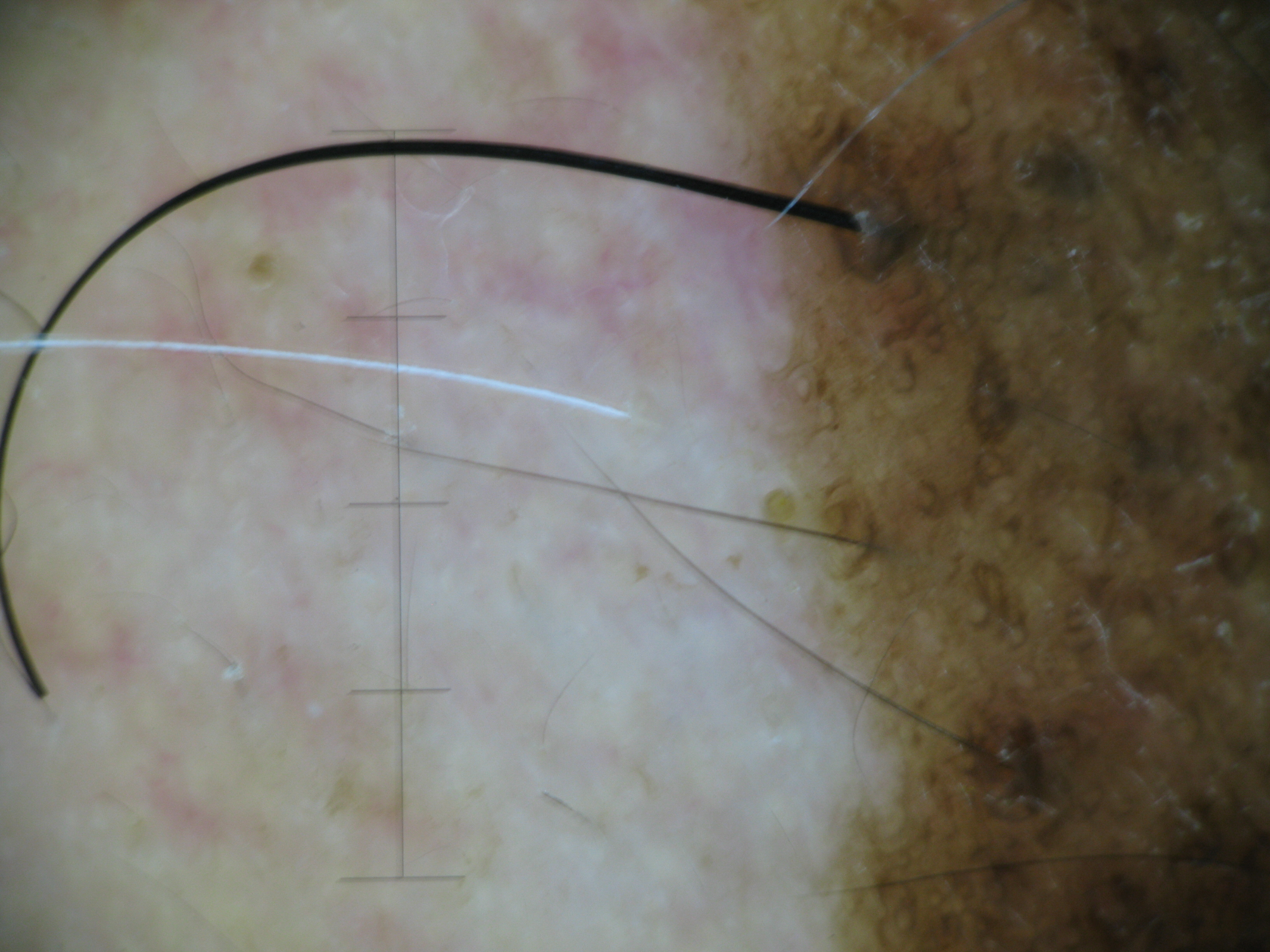| field | value |
|---|---|
| image | dermatoscopy |
| pathology | lentigo maligna (biopsy-proven) |